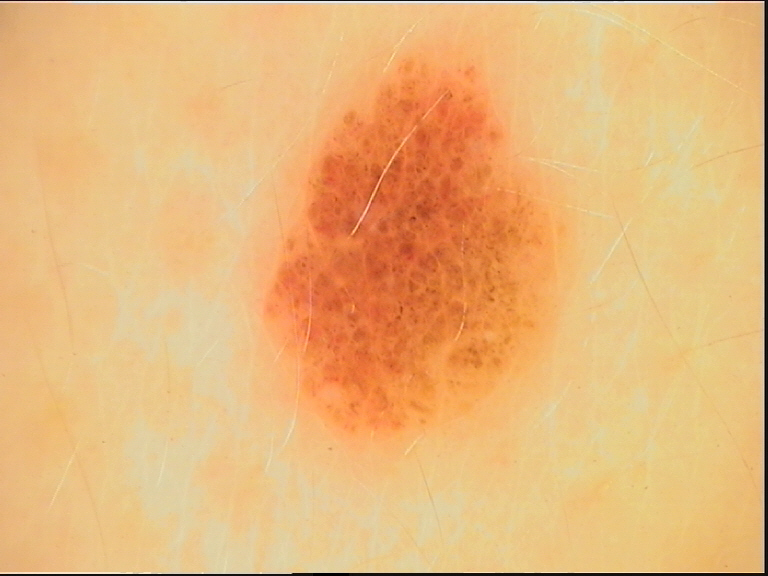{"diagnosis": {"name": "dysplastic compound nevus", "code": "cd", "malignancy": "benign", "super_class": "melanocytic", "confirmation": "expert consensus"}}